Texture is reported as flat, lay graders estimated Monk Skin Tone 4 (US pool) or 3 (India pool), the contributor reports darkening, reported duration is three to twelve months, the photo was captured at an angle, self-categorized by the patient as a growth or mole, the affected area is the top or side of the foot and leg, the contributor is a male aged 40–49.
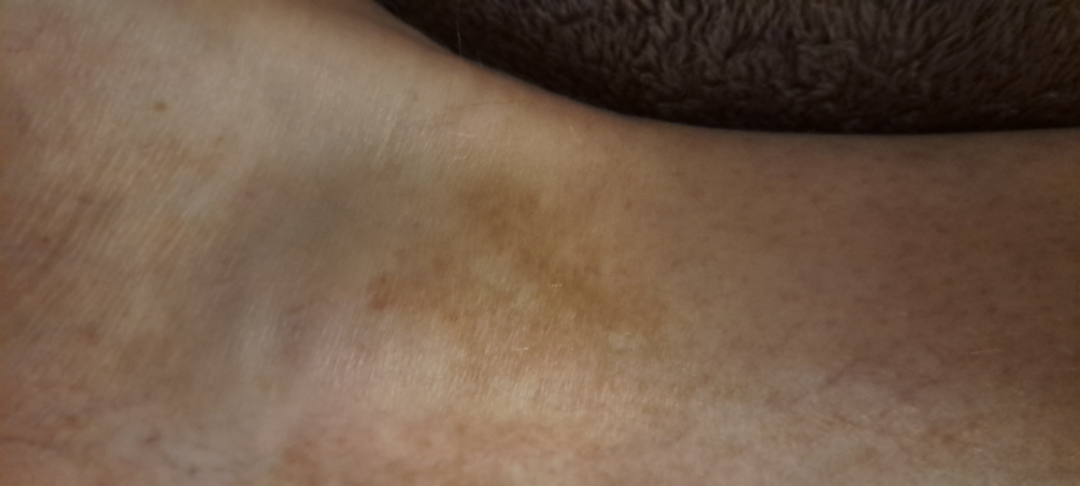On dermatologist assessment of the image: the differential, in no particular order, includes Stasis Dermatitis, Pigmented purpuric eruption and Hemosiderin pigmentation of skin due to venous insufficiency.